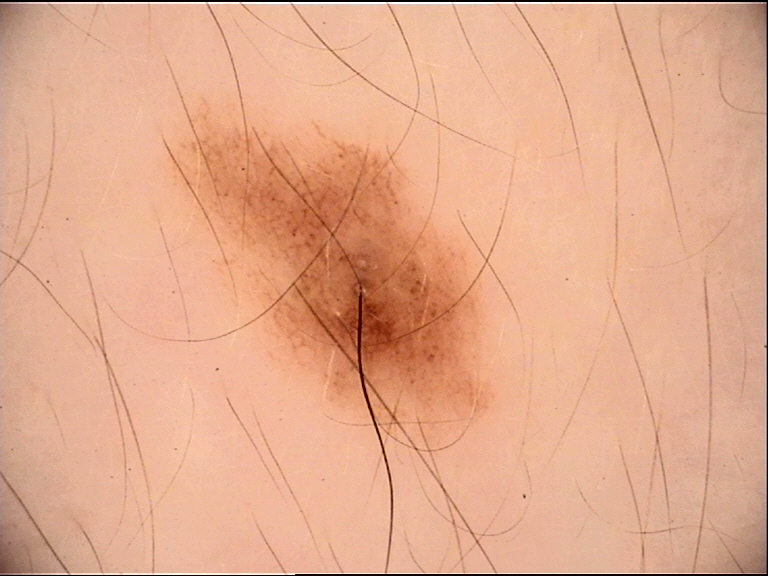* diagnostic label — compound nevus (expert consensus)